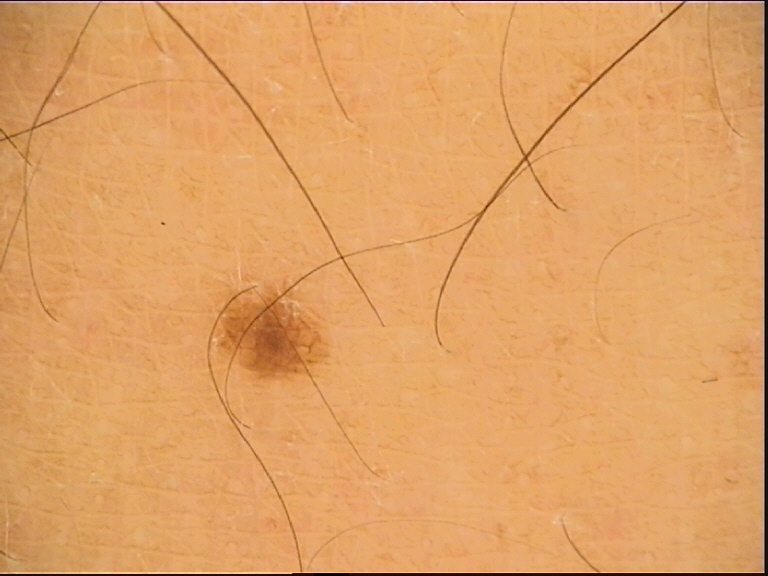image type=dermoscopy; label=dysplastic junctional nevus (expert consensus).